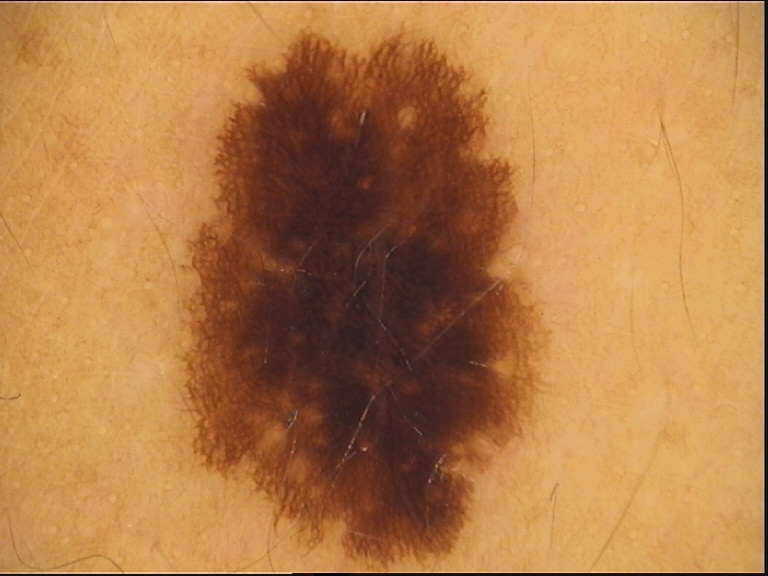Case:
• image · dermatoscopy
• assessment · dysplastic junctional nevus (expert consensus)